A skin lesion imaged with a dermatoscope.
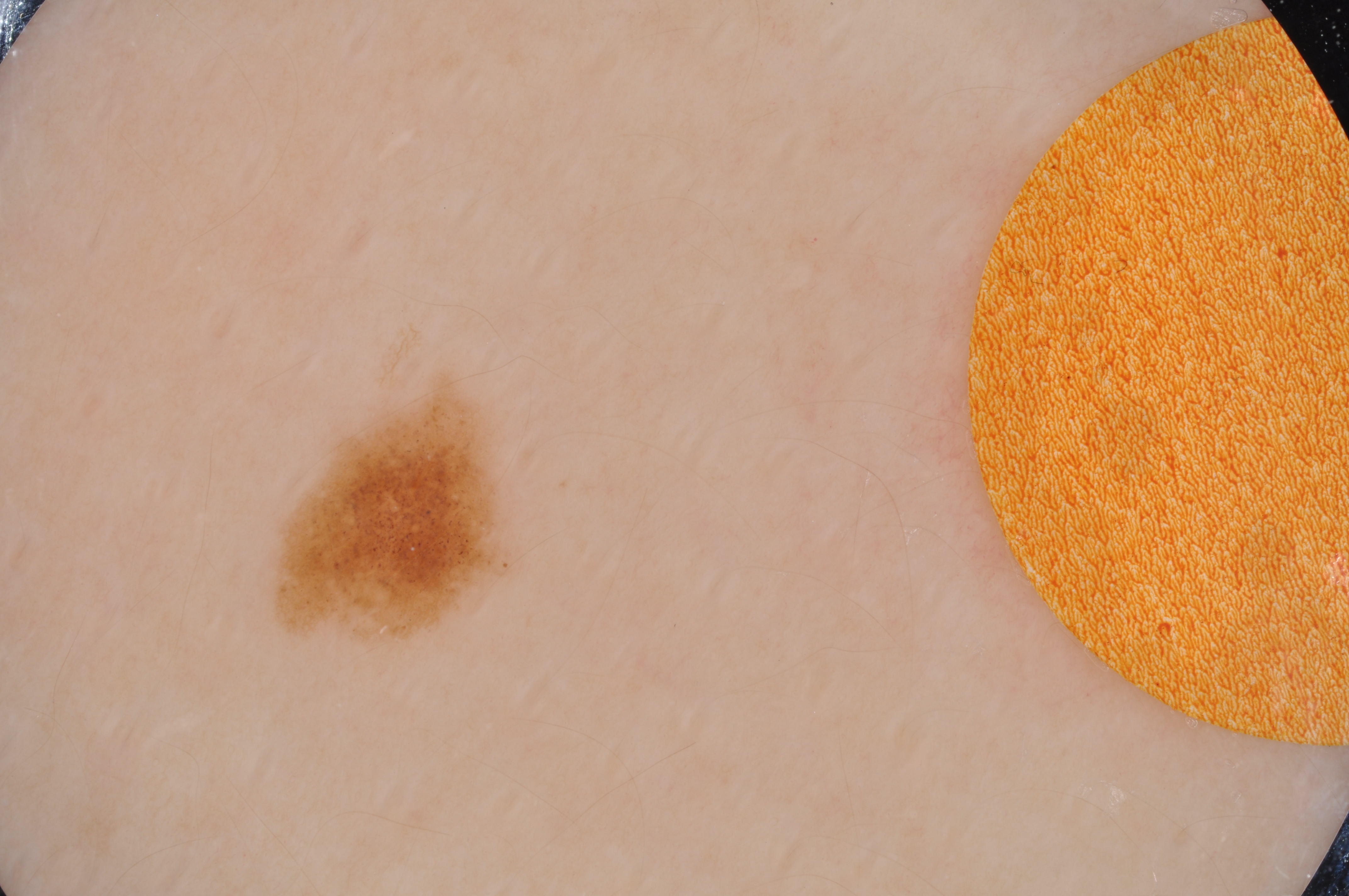lesion bbox: <bbox>264, 366, 526, 662</bbox> | lesion size: small | absent dermoscopic features: globules and streaks | diagnostic label: a benign lesion.